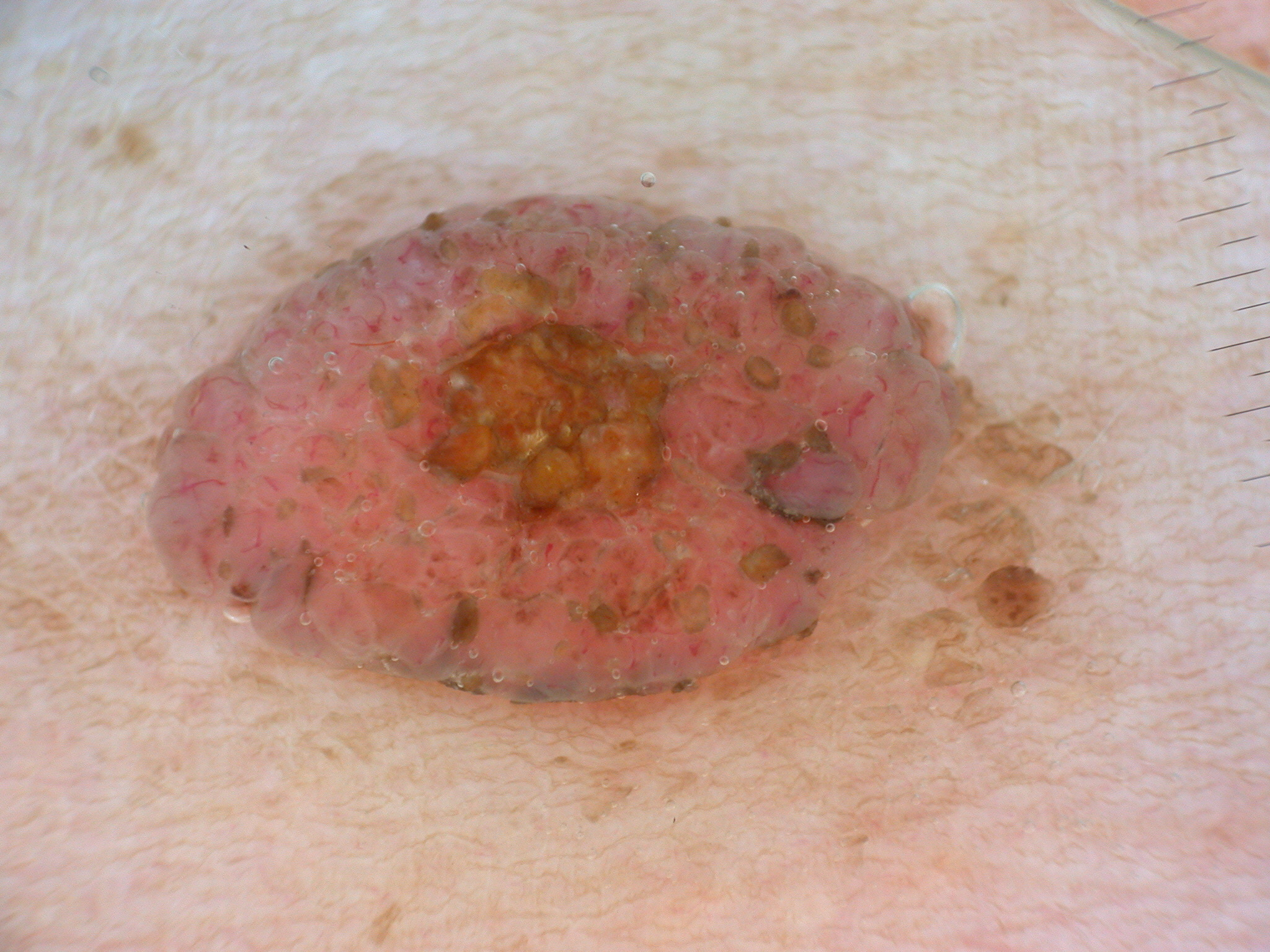image type = dermoscopic image; lesion bbox = <box>141, 189, 1129, 855</box>; diagnosis = a melanocytic nevus, a benign skin lesion.